On a questionnaire the patient reported a history of sunbed use. Numerous moles by the patient's own estimate. The patient says their skin reddens with sun exposure. A female subject 26 years old. Imaged for a research study, with no referral diagnosis recorded — 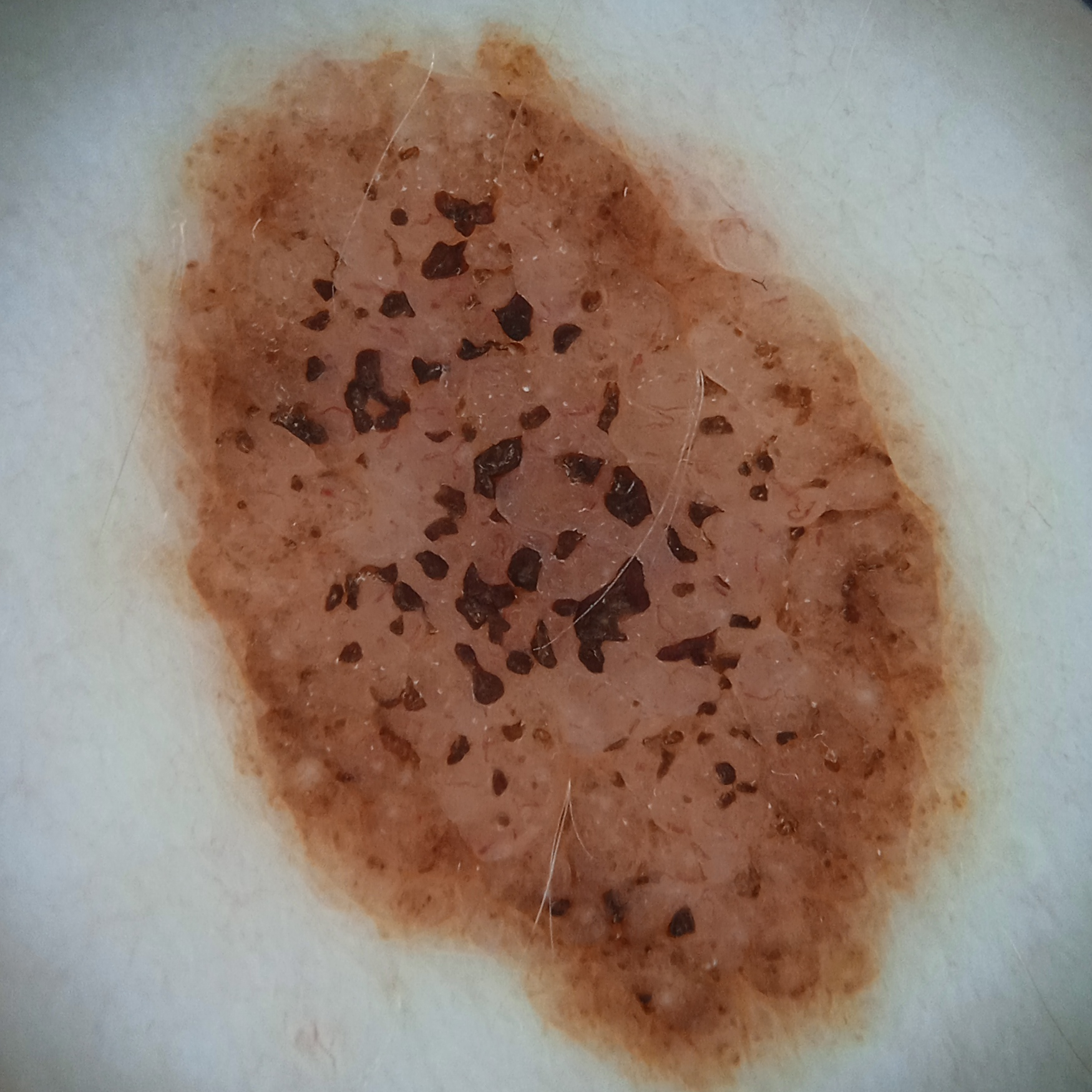The lesion is located on the torso.
The lesion is about 12.1 mm across.
The four-dermatologist consensus diagnosis was a melanocytic nevus; there was some disagreement among the reviewers; the reviewers were fairly confident; an alternative consideration was a seborrheic keratosis.